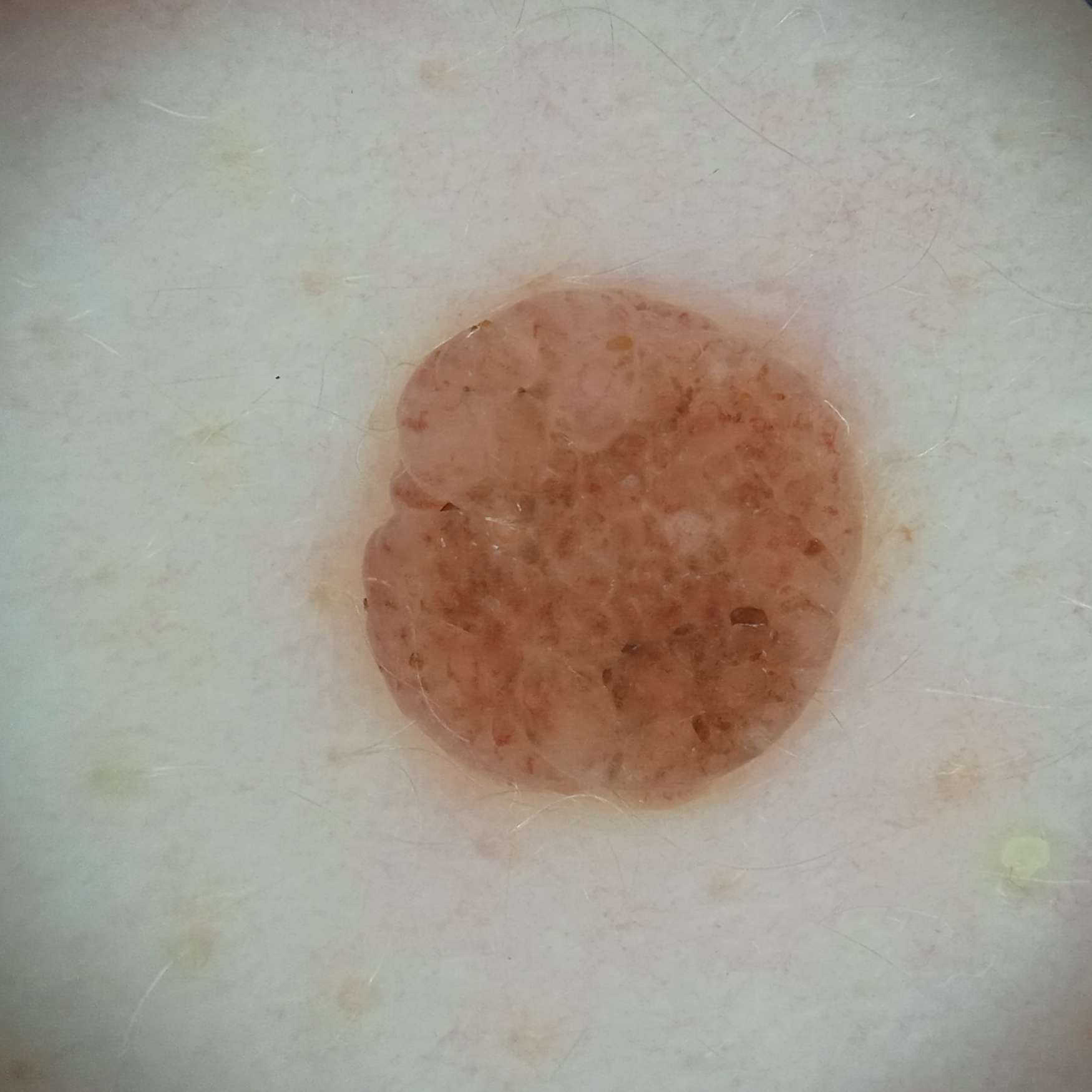By self-report, a history of sunbed use.
The patient describes having numerous moles.
The patient says their skin reddens with sun exposure.
Acquired for a research image collection, with no referral diagnosis.
A dermoscopy image of a skin lesion.
The lesion is on the back.
The lesion measures approximately 5.6 mm.
The diagnostic impression was a melanocytic nevus.